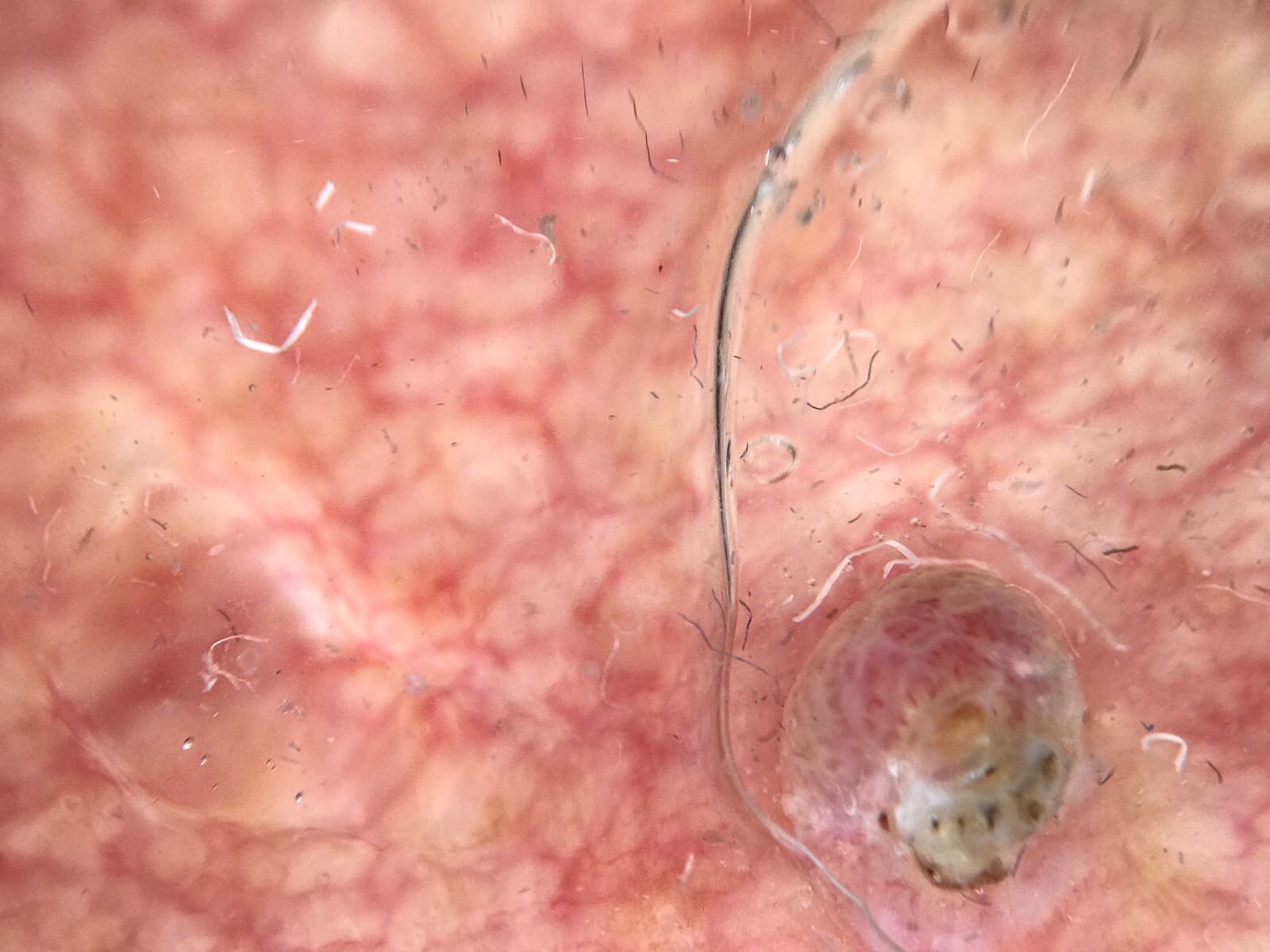modality — dermatoscopy
class — squamous cell carcinoma (biopsy-proven)